Dermoscopy of a skin lesion:
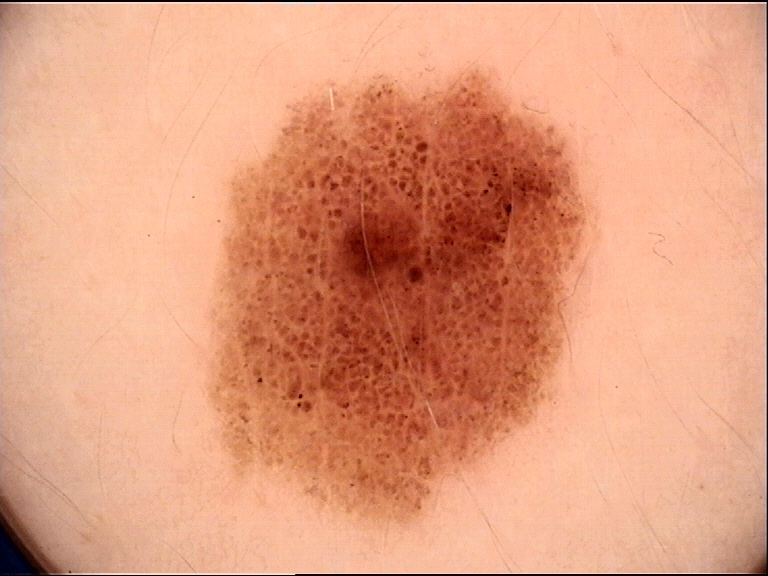Impression:
Diagnosed as a banal lesion — a junctional nevus.